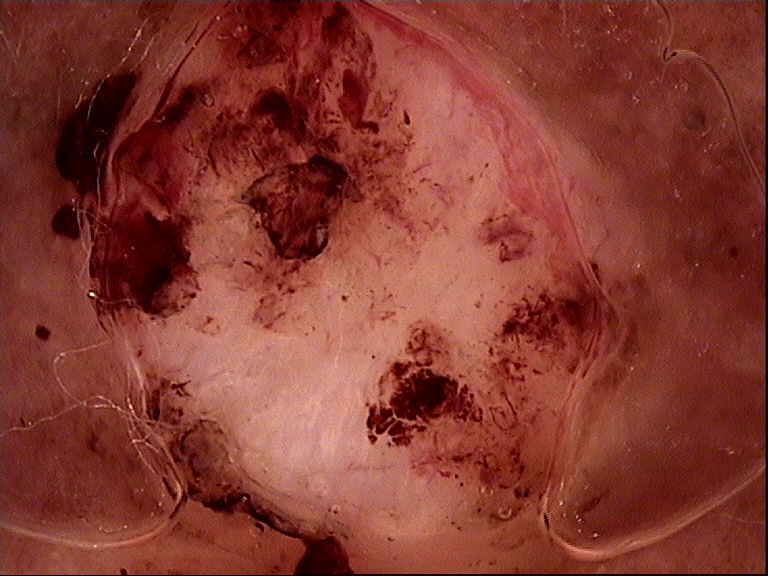Diagnosis: Histopathology confirmed a basal cell carcinoma.